A dermoscopic image of a skin lesion. A female subject, aged around 65: 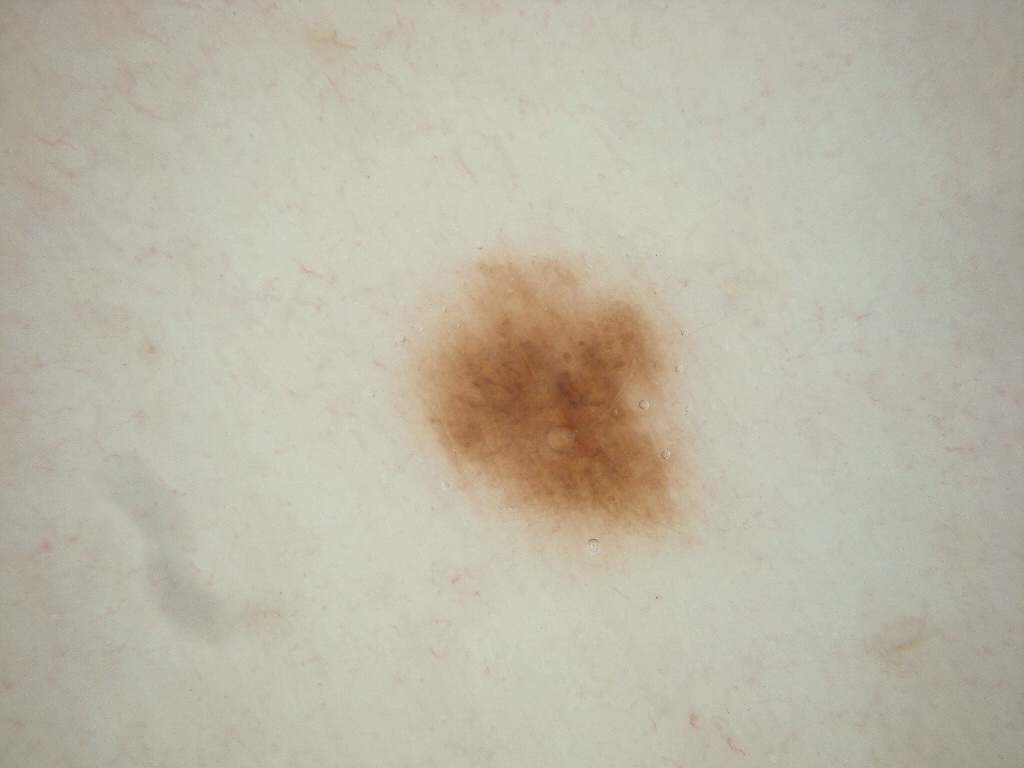{"dermoscopic_features": {"present": [], "absent": ["globules", "streaks", "milia-like cysts", "negative network", "pigment network"]}, "lesion_extent": {"approx_field_fraction_pct": 8}, "lesion_location": {"bbox_xyxy": [403, 255, 696, 548]}, "diagnosis": {"name": "melanocytic nevus", "malignancy": "benign", "lineage": "melanocytic", "provenance": "clinical"}}